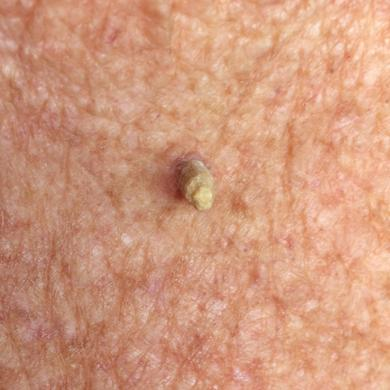A female patient 71 years of age. By history, prior malignancy (patient or family) and no tobacco use. The patient was assessed as Fitzpatrick III. The lesion was found on the chest. Measuring about 4 × 3 mm. On biopsy, the diagnosis was a lesion of indeterminate malignant potential — an actinic keratosis.